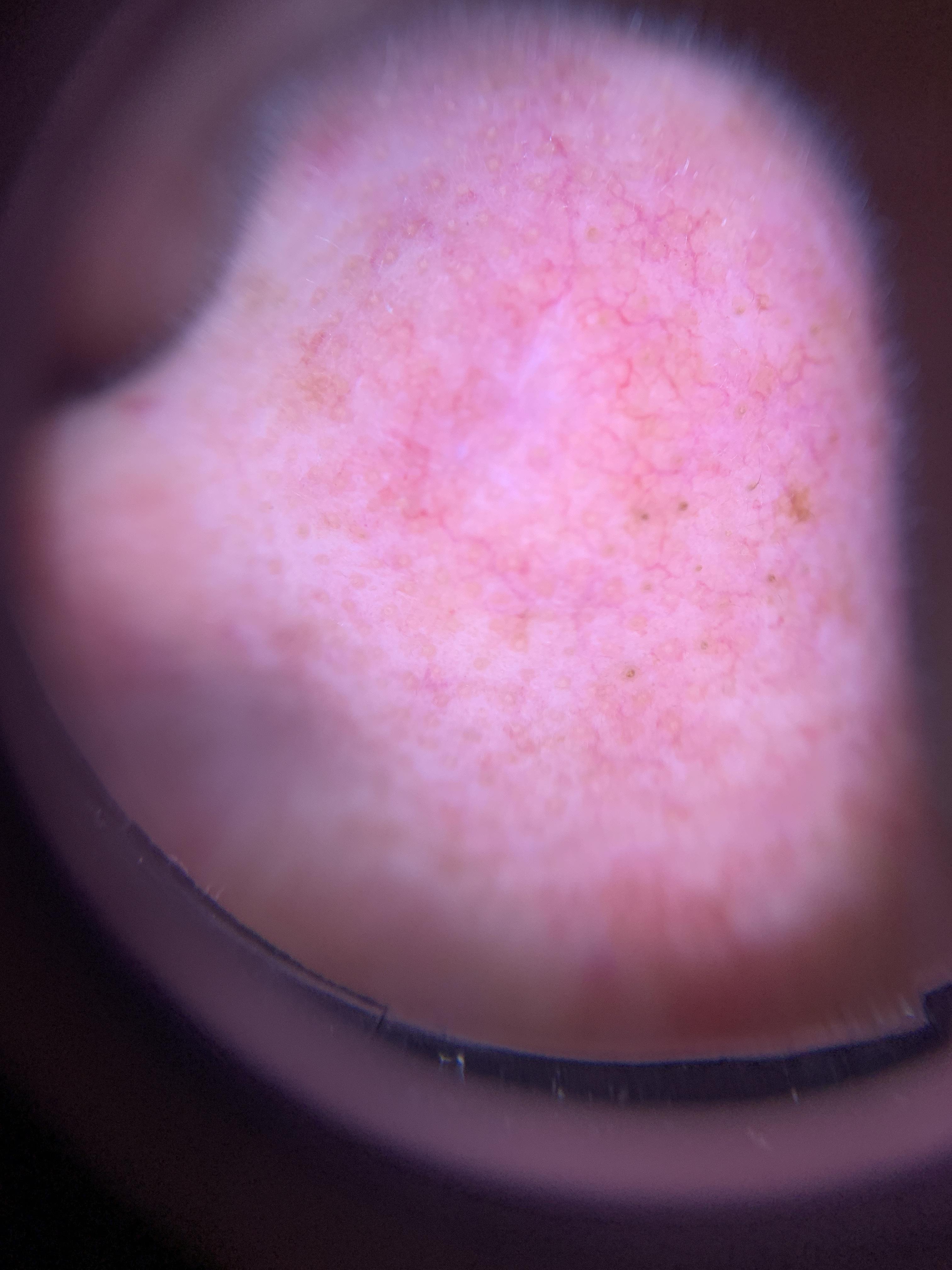Findings:
• skin phototype · II
• subject · female, aged 63-67
• image · contact-polarized dermoscopy
• site · the head or neck
• pathology · Basal cell carcinoma (biopsy-proven)